The leg, front of the torso, arm, head or neck, back of the hand and palm are involved · the lesion is described as rough or flaky, raised or bumpy and fluid-filled · this image was taken at an angle · symptoms reported: burning, enlargement, pain, bothersome appearance, bleeding, itching and darkening:
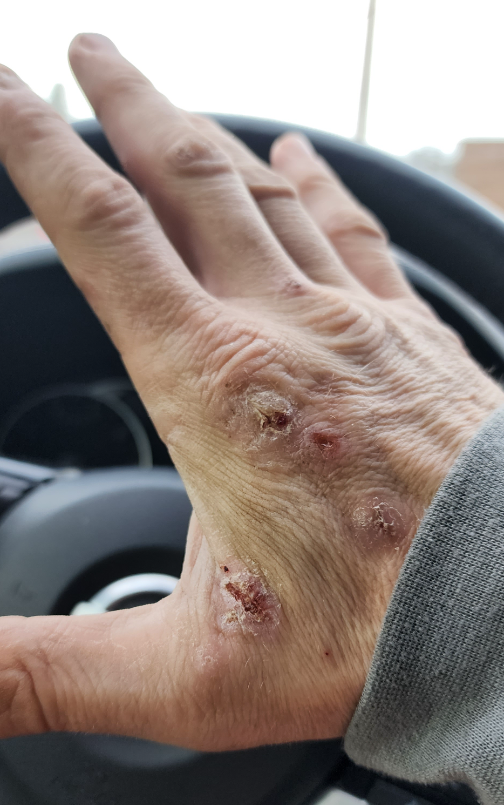<dermatology_case>
  <differential>
    <leading>Inflicted skin lesions</leading>
    <considered>Acne</considered>
    <unlikely>Bacterial pyoderma</unlikely>
  </differential>
</dermatology_case>